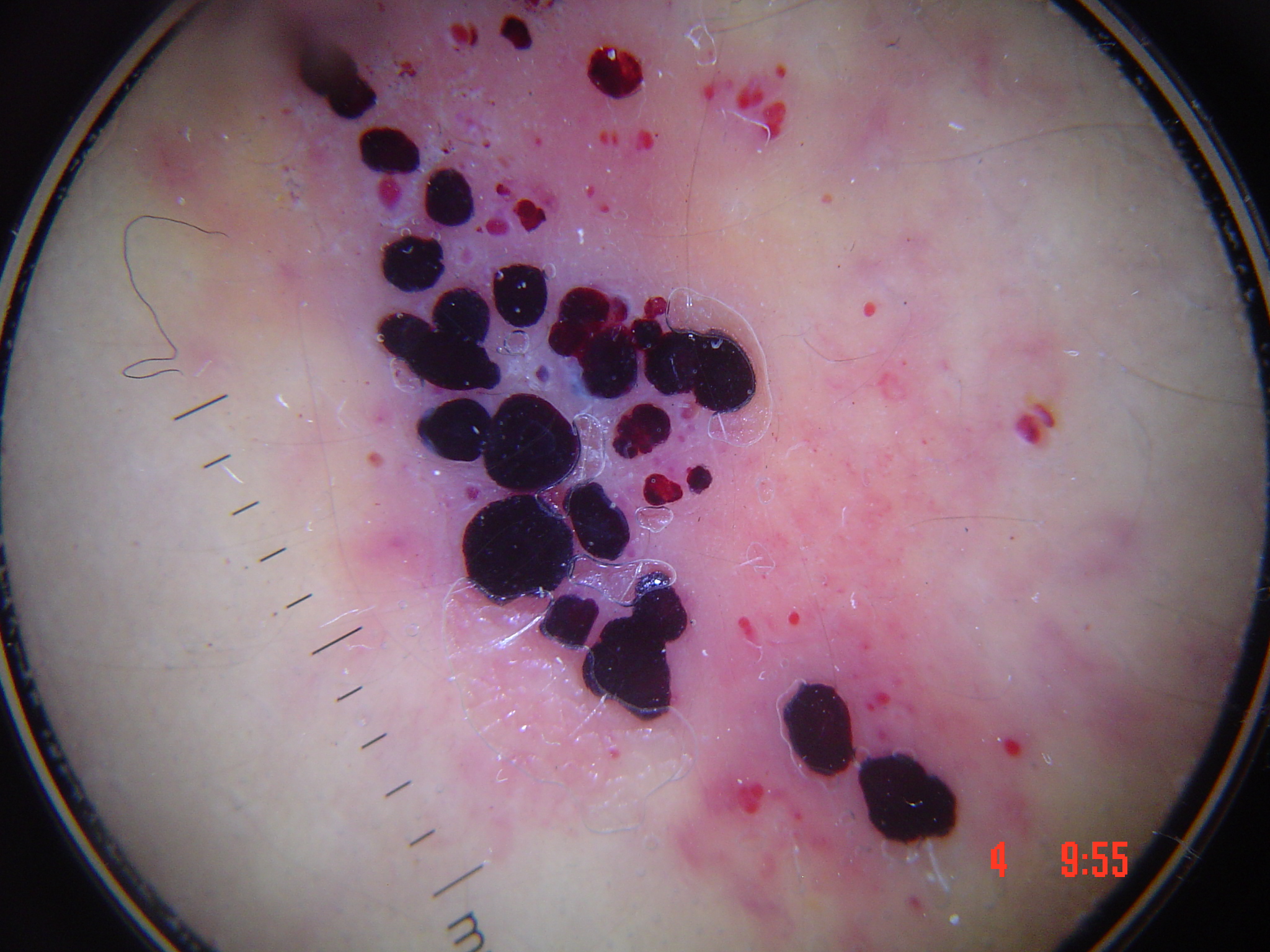imaging: dermatoscopy, class: angiokeratoma (expert consensus).